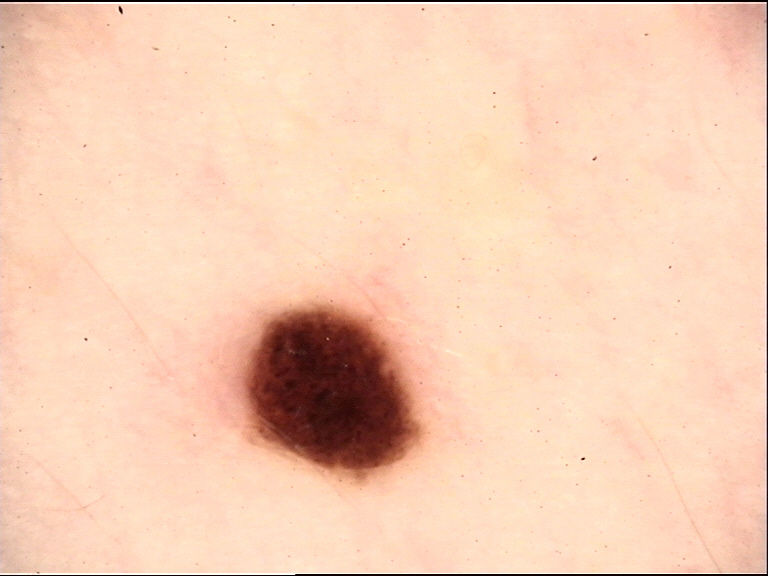image type: dermatoscopy
diagnosis: dysplastic compound nevus (expert consensus)